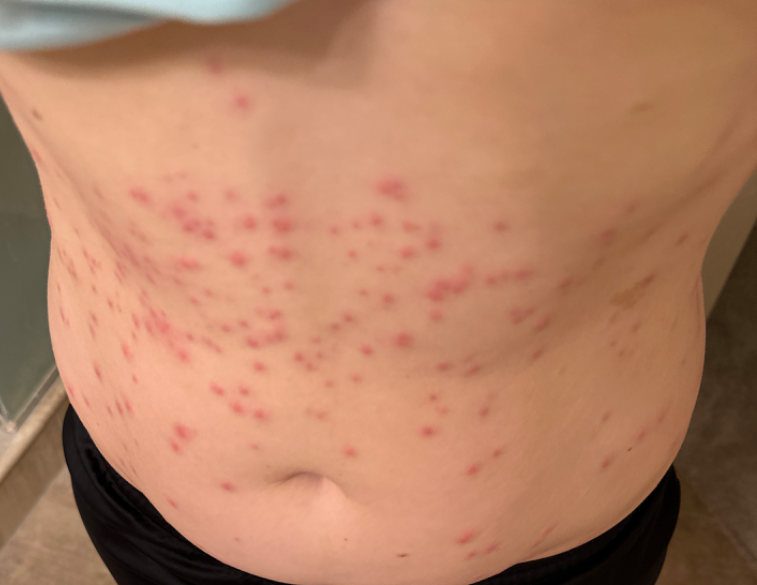Background: The photo was captured at an angle. The patient indicates the lesion is raised or bumpy. The front of the torso, leg, arm and back of the torso are involved. The lesion is associated with bothersome appearance and itching. The patient considered this a rash. Findings: On teledermatology review, most likely Insect Bite.